This is a close-up image · the affected area is the front of the torso:
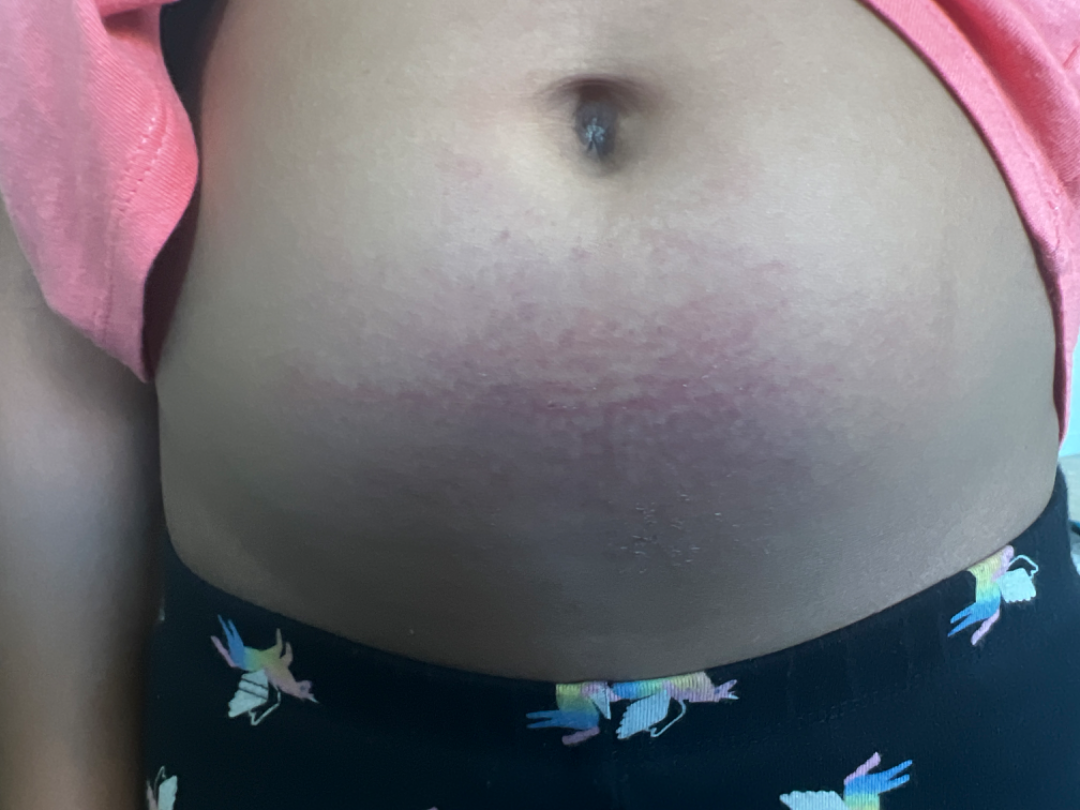symptoms: burning
systemic_symptoms: none reported
patient_category: a rash
duration: about one day
texture: flat
differential:
  tied_lead:
    - Xerosis
    - Allergic Contact Dermatitis
    - Pruritic urticarial papules and plaques of pregnancy